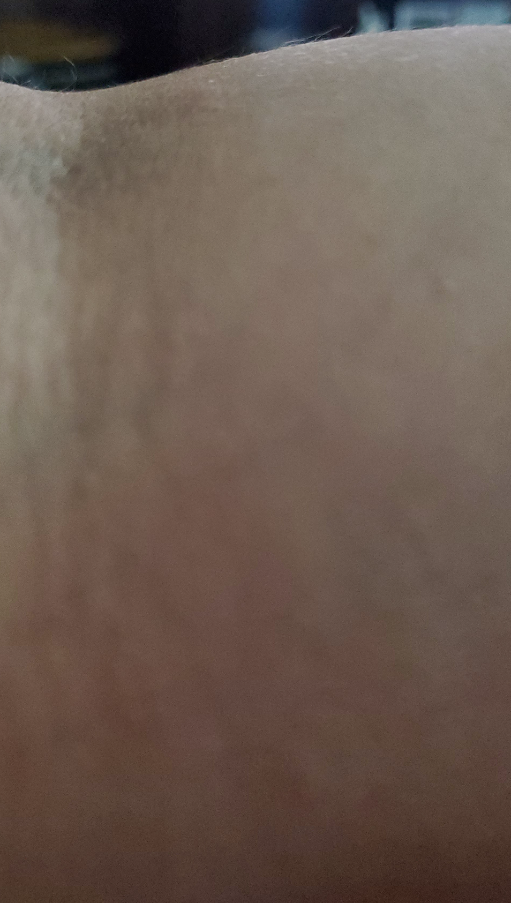Female subject, age 40–49. Located on the arm, front of the torso and back of the torso. The photograph was taken at an angle. On teledermatology review, the leading consideration is Eczema; the differential also includes Acute and chronic dermatitis.